The contributor reports the condition has been present for less than one week · this image was taken at an angle · no associated systemic symptoms reported · the top or side of the foot, leg and arm are involved · the contributor is a female aged 18–29.
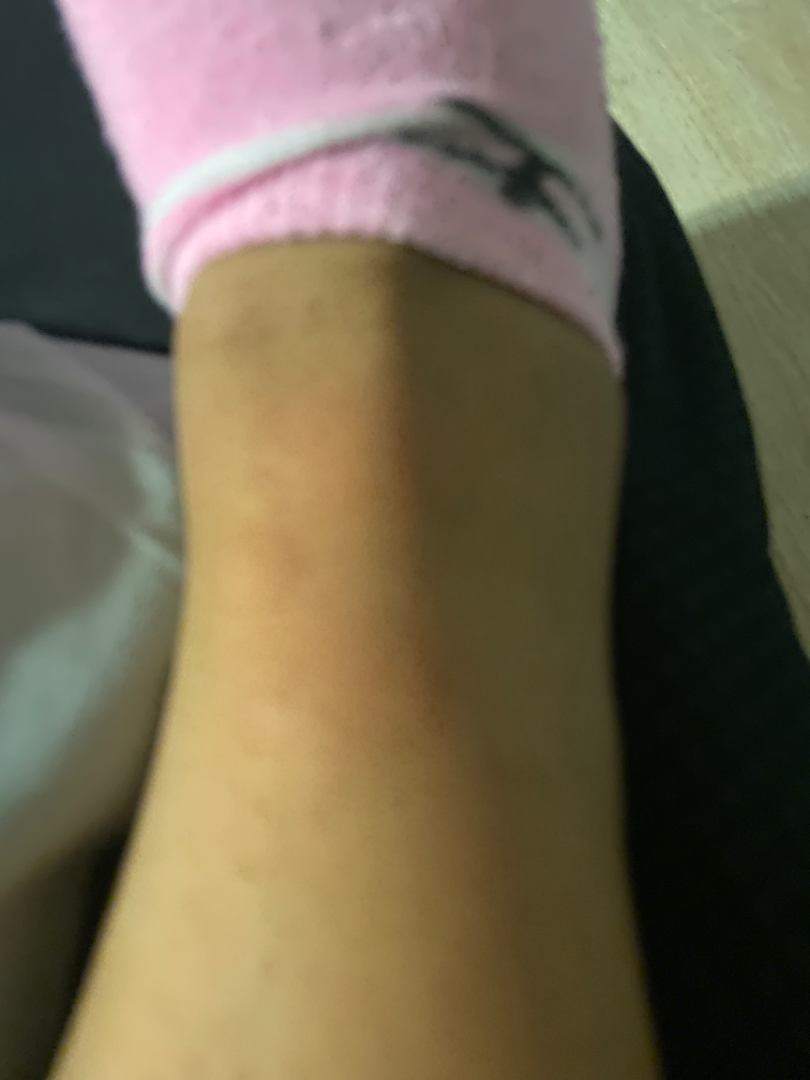assessment — could not be assessed.